Acquired for a research image collection, with no referral diagnosis; a macroscopic clinical photograph of a skin lesion; a male patient 65 years of age; the patient says their skin reddens painfully with sun exposure — 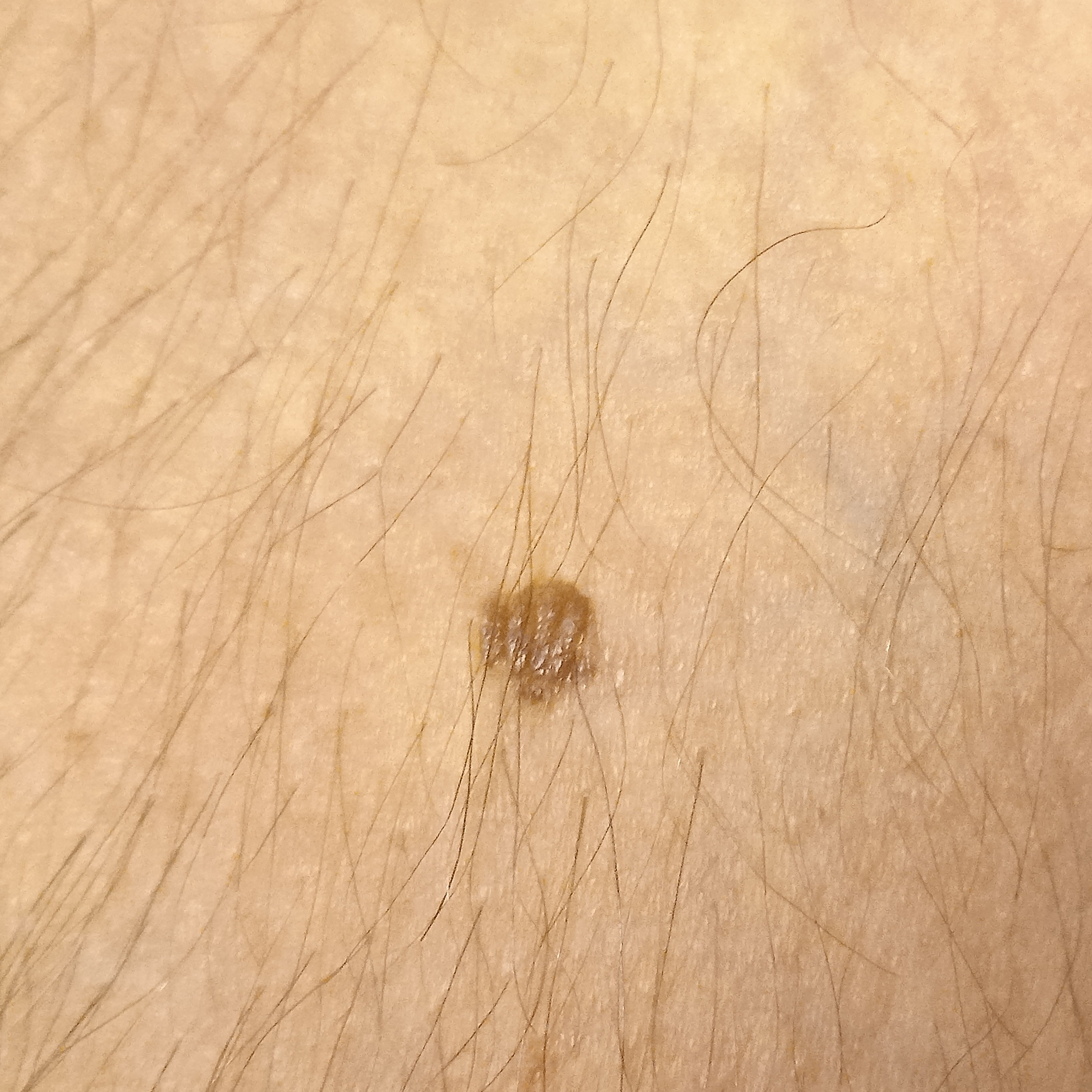The lesion is located on an arm.
The lesion is about 5.5 mm across.
The consensus diagnosis for this lesion was a melanocytic nevus.